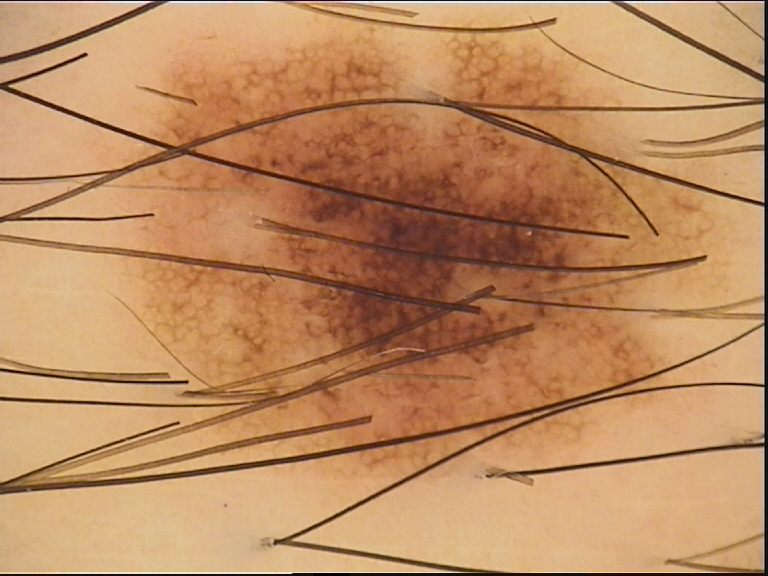image = dermoscopy, assessment = dysplastic junctional nevus (expert consensus).